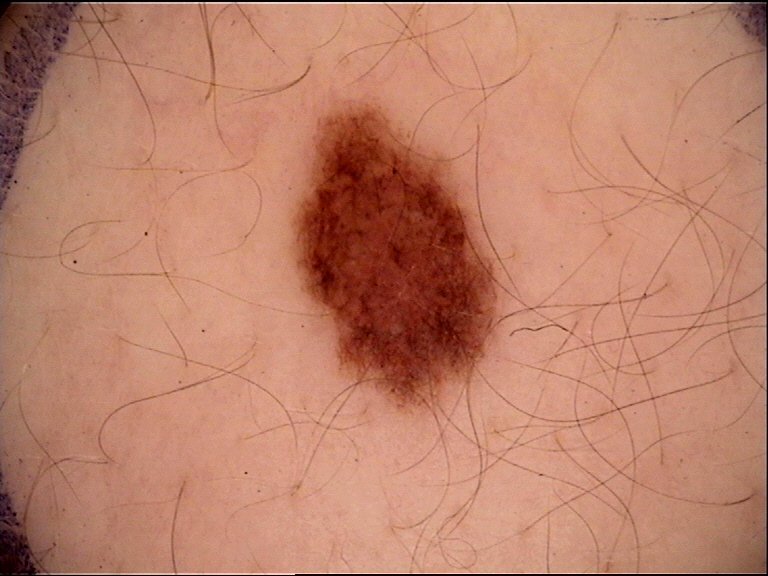Classified as a dysplastic compound nevus.